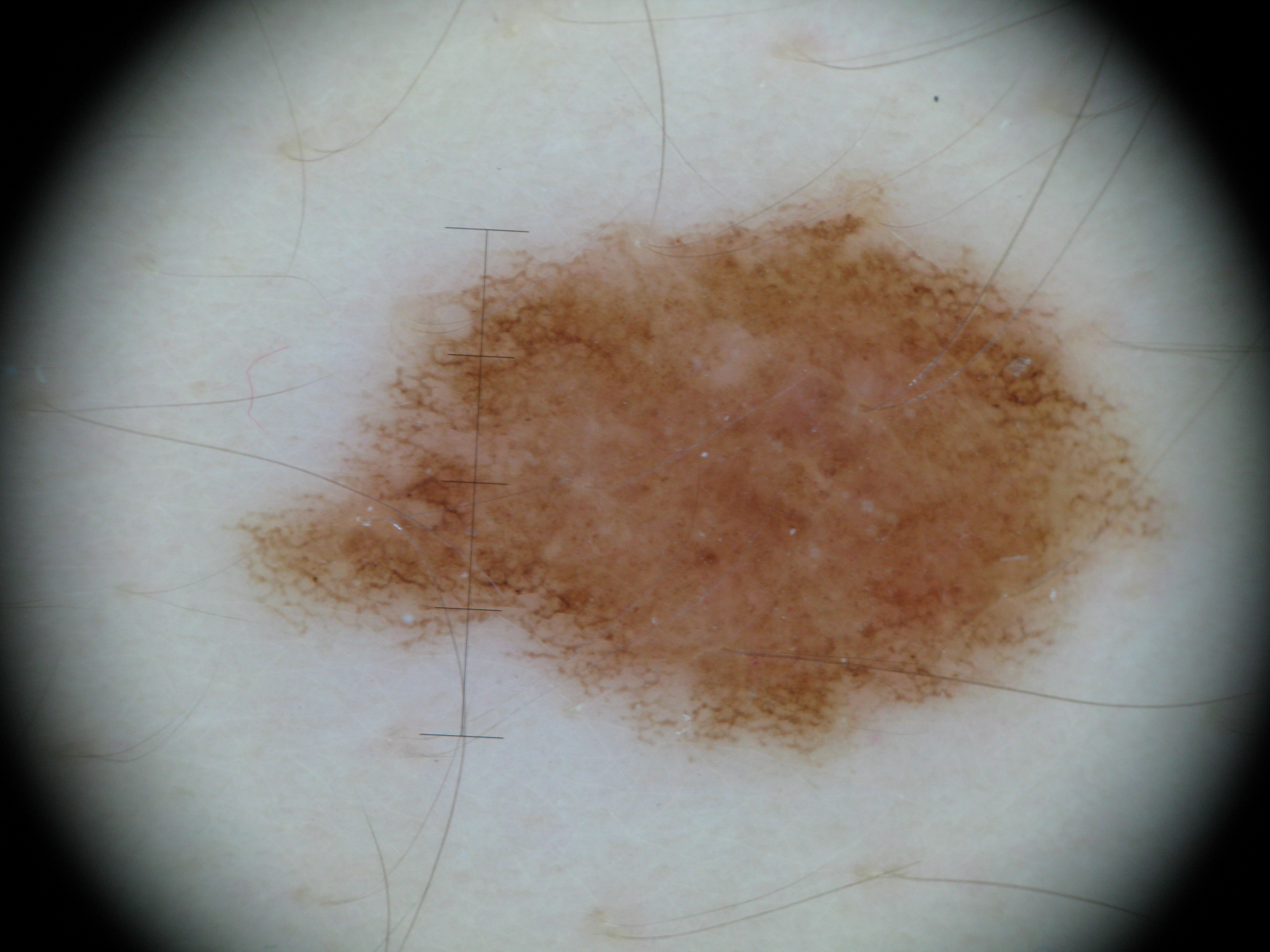A dermoscopic image of a skin lesion. Diagnosed as a benign lesion — a dysplastic junctional nevus.